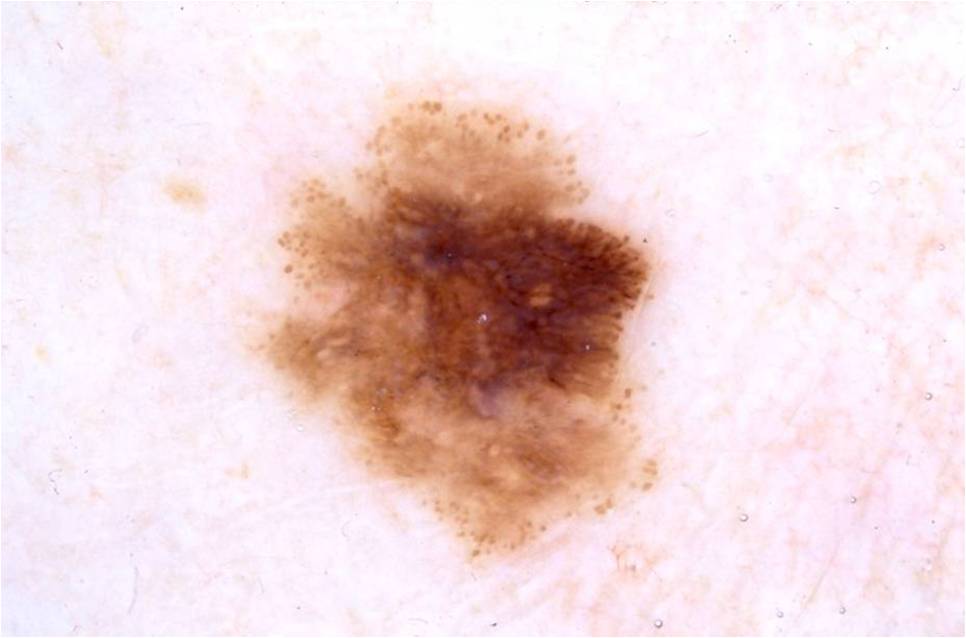image: dermatoscopic image of a skin lesion; location: 240 97 665 560; extent: moderate; assessment: a malignant skin lesion.